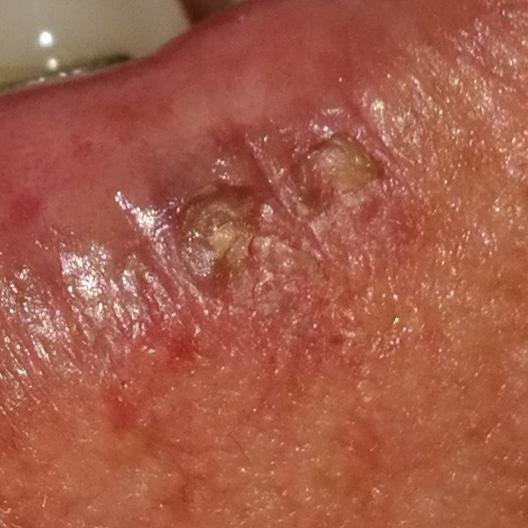patient:
  age: 38
  gender: male
risk_factors:
  positive:
    - prior cancer (patient or family)
    - pesticide exposure
    - alcohol use
  negative:
    - smoking
    - prior skin cancer (patient or family)
image: clinical photo
skin_type: III
lesion_location: a lip
symptoms:
  present:
    - elevation
    - bleeding
    - itching
    - growth
    - pain
  absent:
    - change in appearance
diagnosis:
  name: actinic keratosis
  code: ACK
  malignancy: indeterminate
  confirmation: histopathology